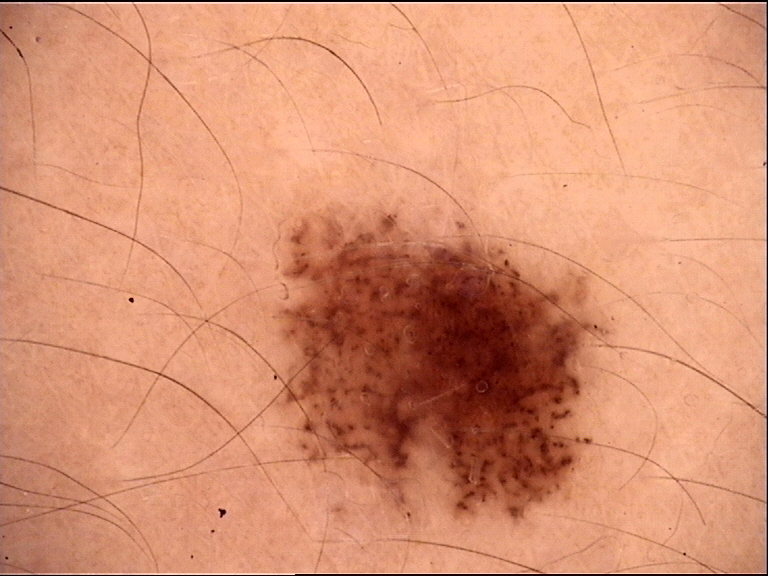{"diagnosis": {"name": "dysplastic junctional nevus", "code": "jd", "malignancy": "benign", "super_class": "melanocytic", "confirmation": "expert consensus"}}